Dermoscopy of a skin lesion.
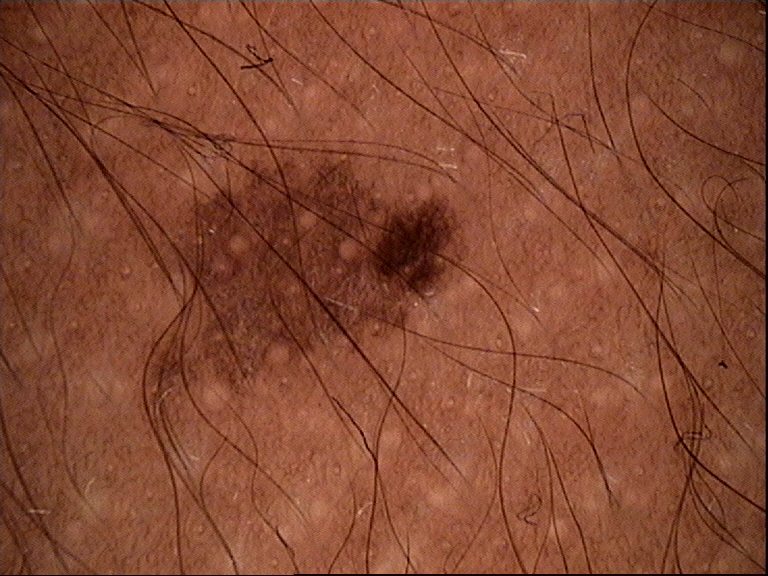Impression: Classified as a dysplastic junctional nevus.